A dermoscopic view of a skin lesion · the subject is a male in their 70s:
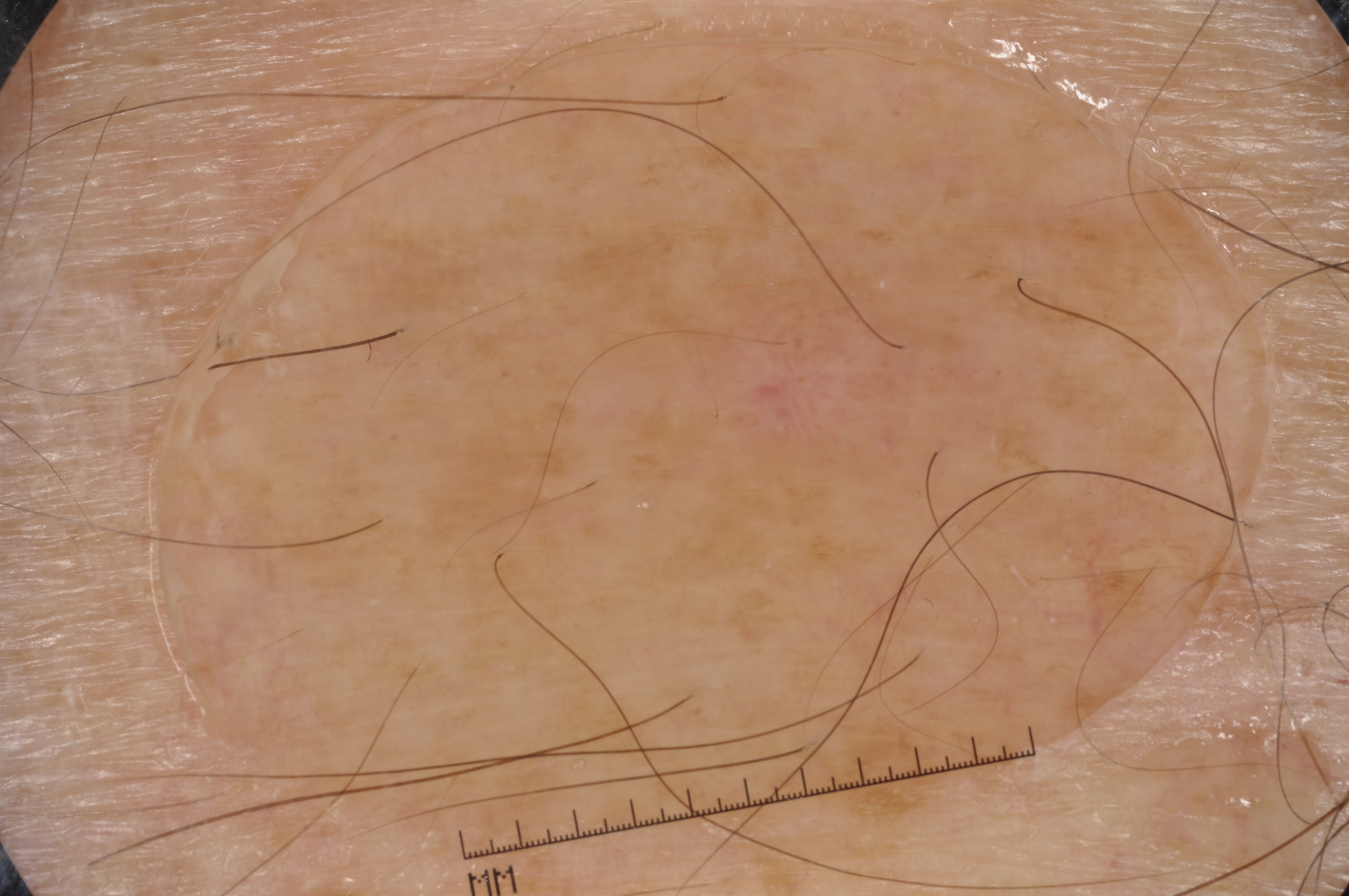Findings:
A small lesion within a wider field of skin. Dermoscopic review identifies milia-like cysts; no negative network, streaks, or pigment network. The lesion occupies the region [688, 291, 1006, 477].
Impression:
Diagnosed as a melanocytic nevus, a benign lesion.